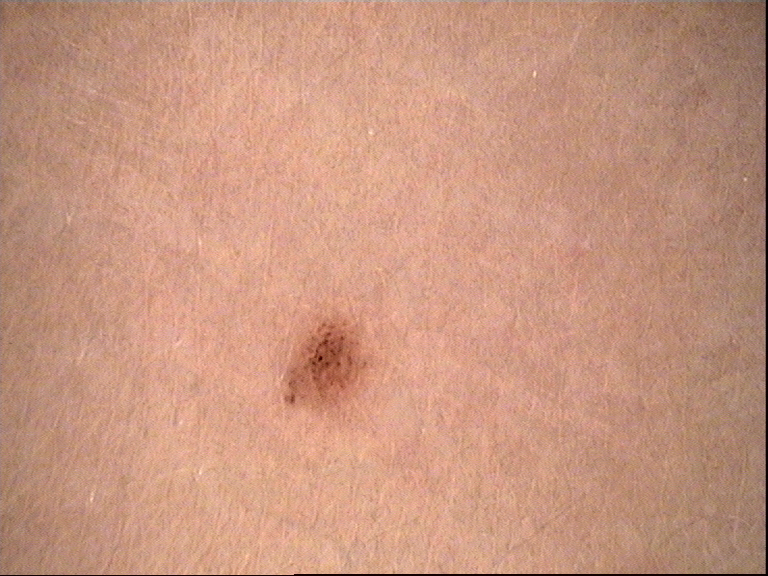A dermoscopic photograph of a skin lesion. The diagnostic label was a benign lesion — a dysplastic junctional nevus.